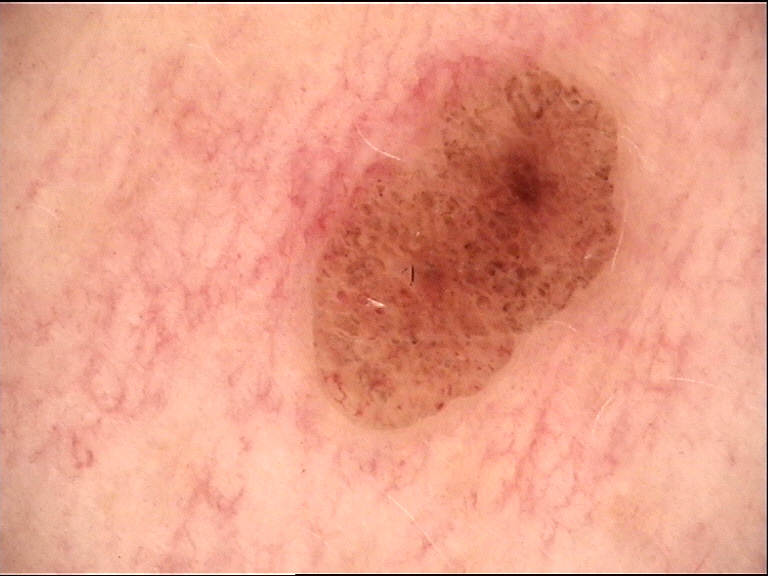imaging: dermoscopy | lesion type: banal | diagnostic label: dermal nevus (expert consensus).